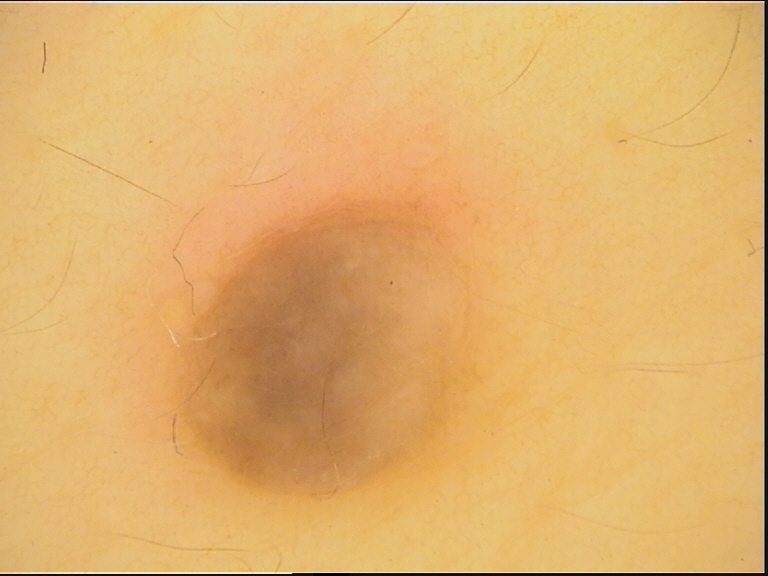The architecture is that of a dermal, banal lesion. Labeled as a blue nevus.